A close-up photograph; the lesion involves the back of the hand; self-categorized by the patient as a rash; the condition has been present for less than one week; the patient reports the lesion is rough or flaky; male contributor, age 18–29 — 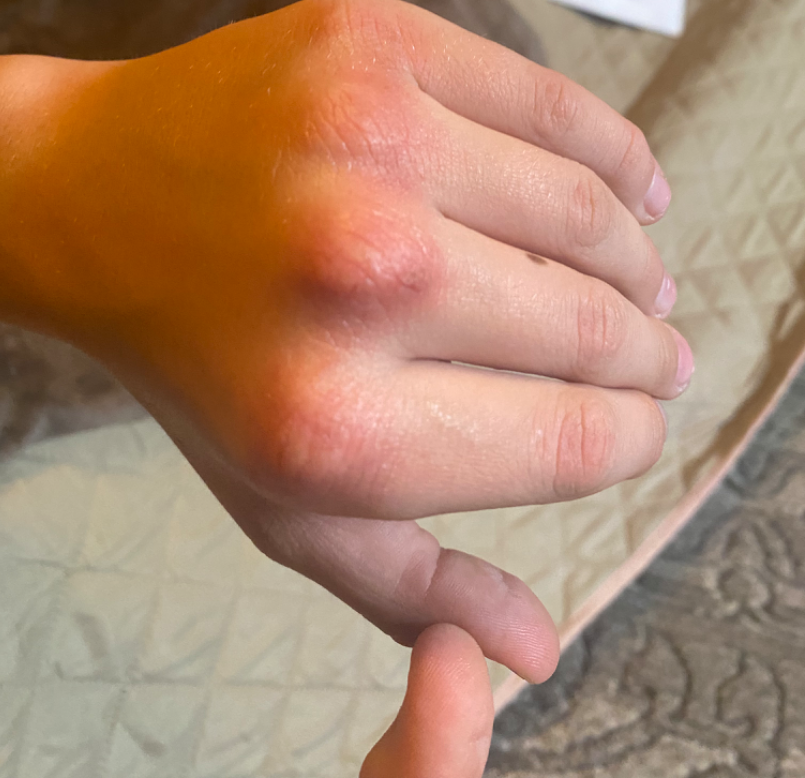| key | value |
|---|---|
| differential diagnosis | Eczema (0.55); Irritant Contact Dermatitis (0.27); Autoimmune diseases affecting skin (0.18) |